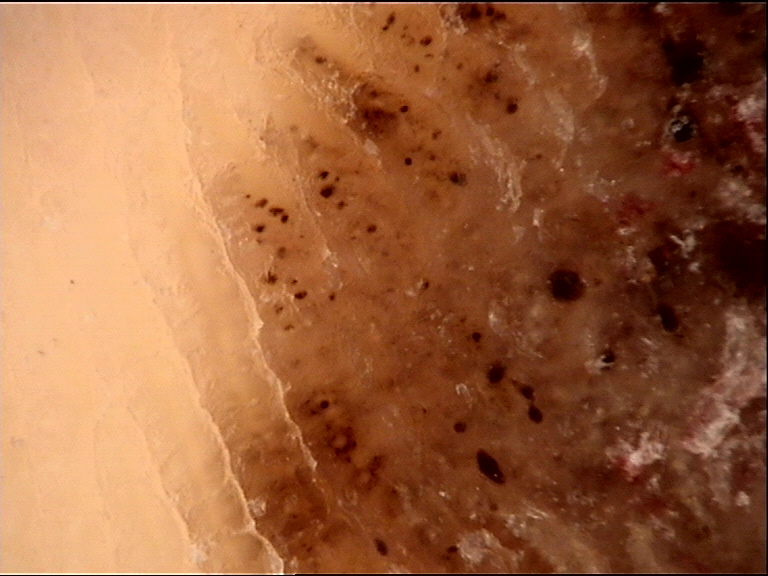Dermoscopy of a skin lesion. The biopsy diagnosis was a malignant lesion — an acral nodular melanoma.